A clinical close-up photograph of a skin lesion:
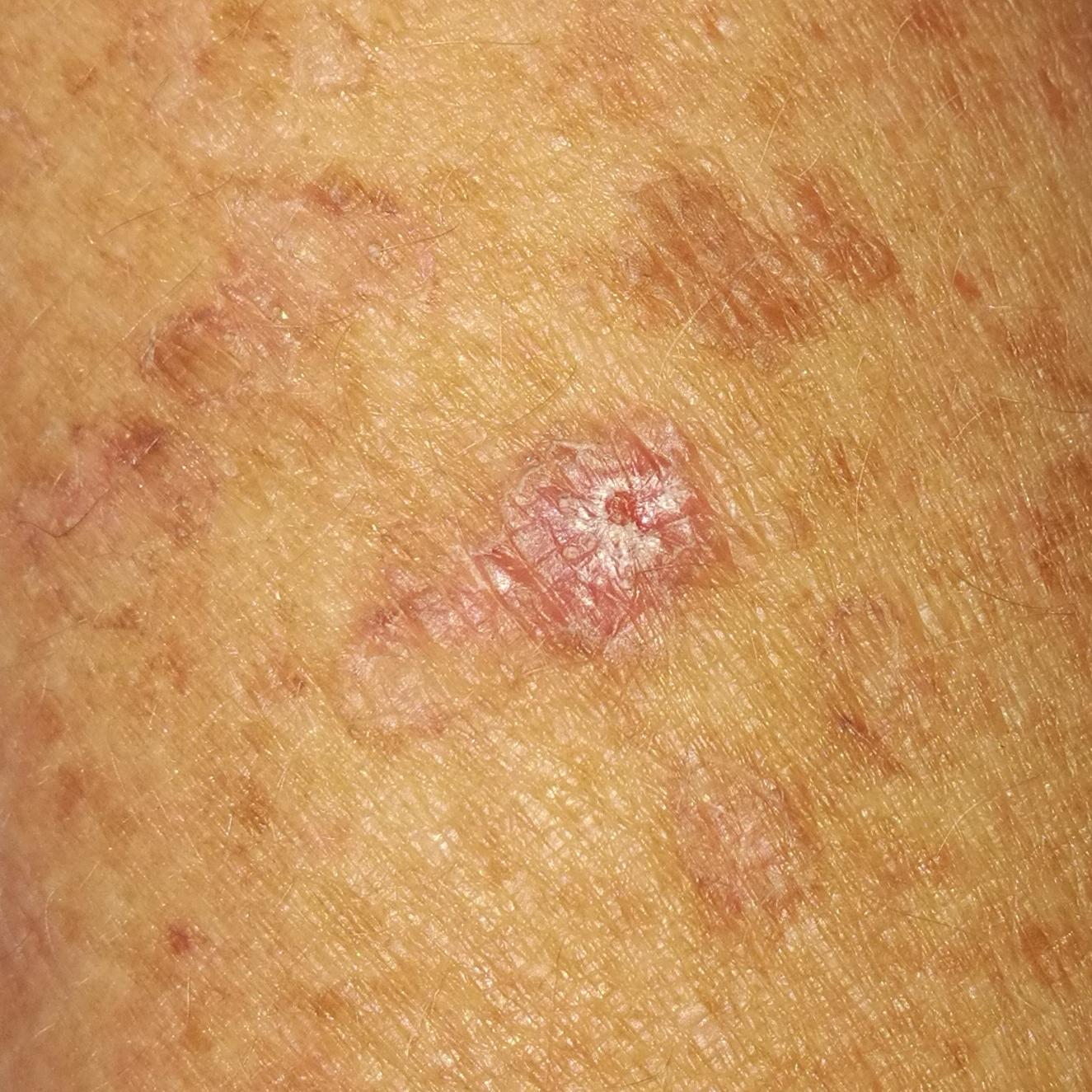- location — a forearm
- diagnostic label — actinic keratosis (clinical consensus)